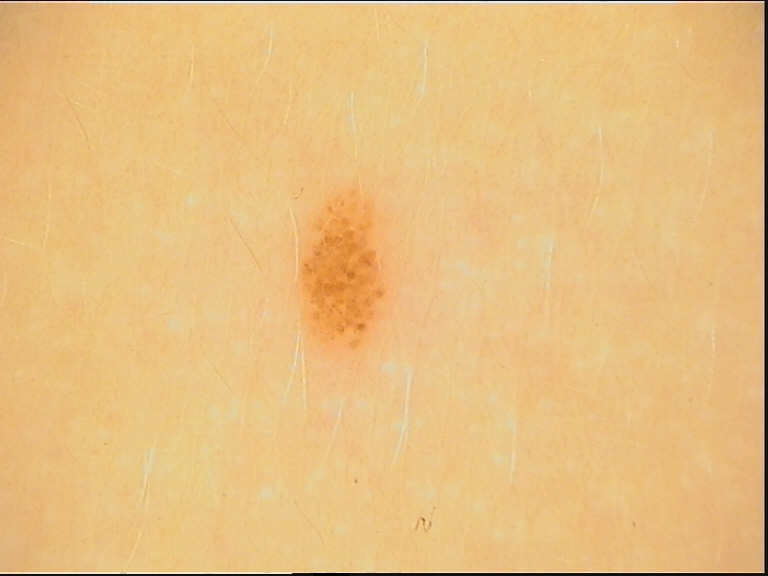image type = dermoscopy; assessment = dysplastic junctional nevus (expert consensus).